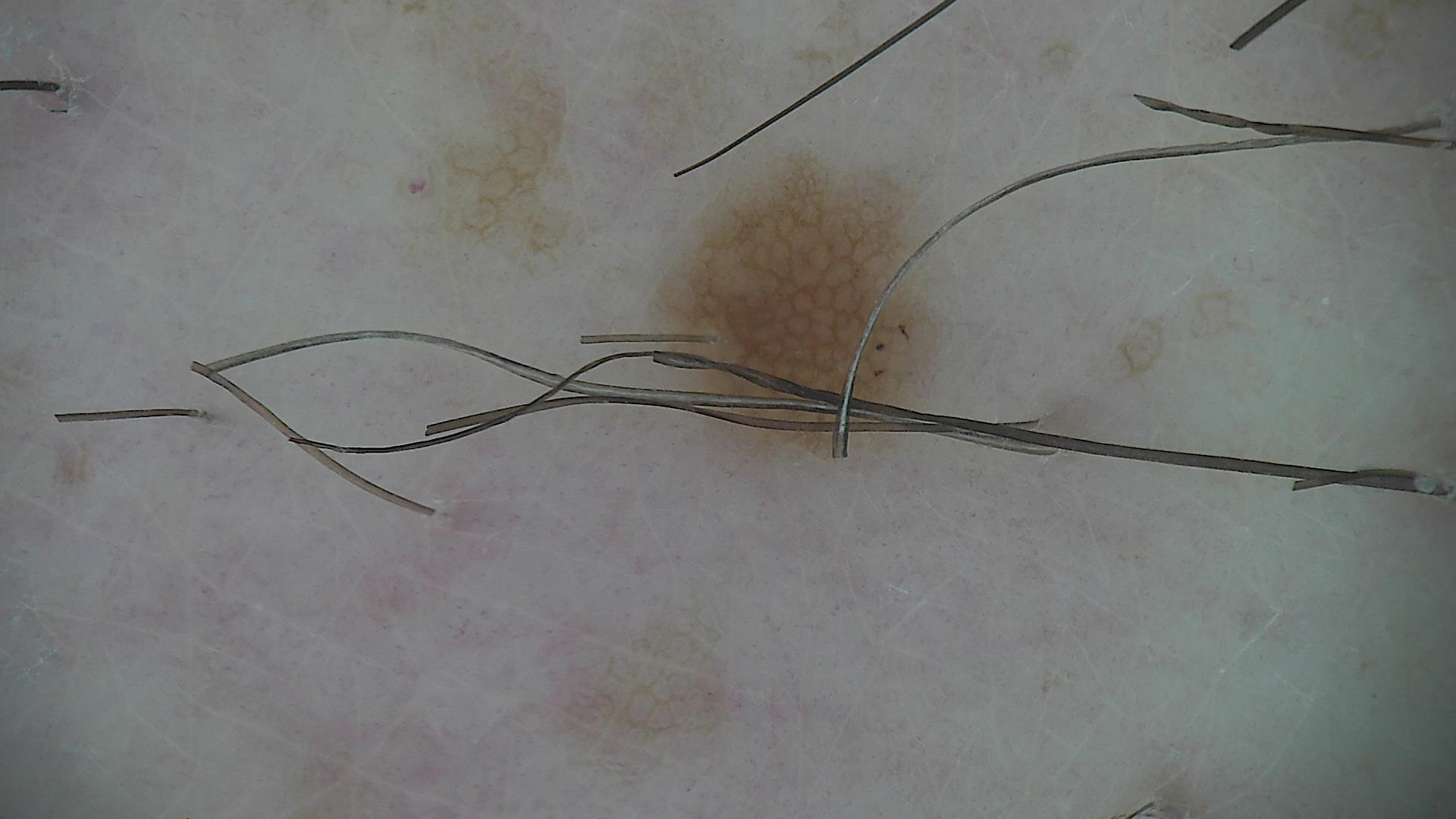image=dermatoscopy | diagnostic label=dysplastic junctional nevus (expert consensus).